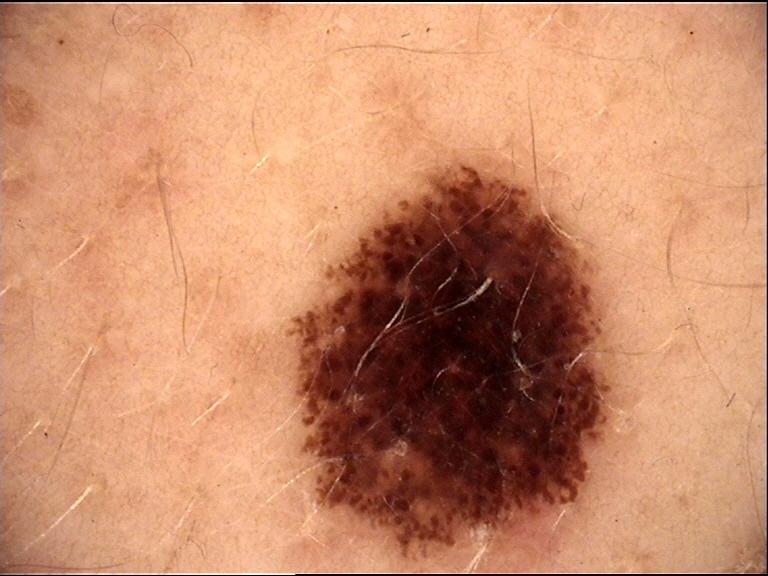image: dermoscopy
lesion_type:
  main_class: banal
  pattern: compound
diagnosis:
  name: compound nevus
  code: cb
  malignancy: benign
  super_class: melanocytic
  confirmation: expert consensus